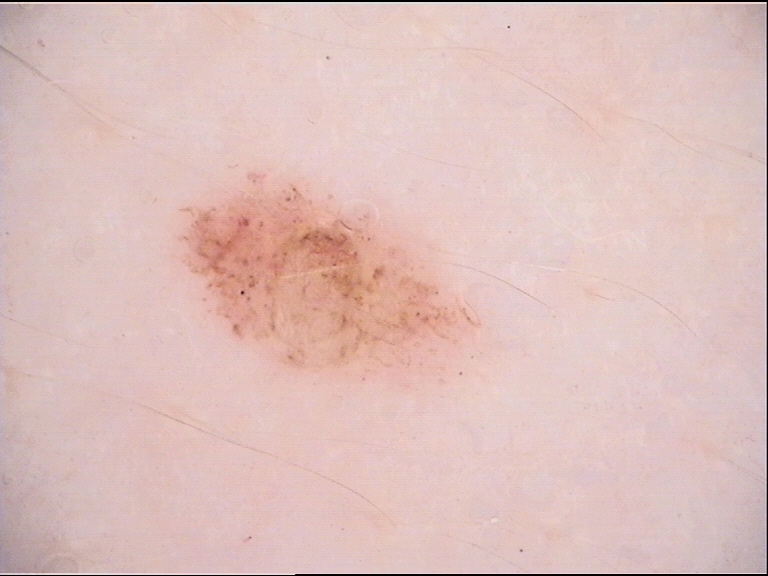image type: dermoscopy, diagnostic label: dysplastic junctional nevus (expert consensus).